A dermoscopic photograph of a skin lesion.
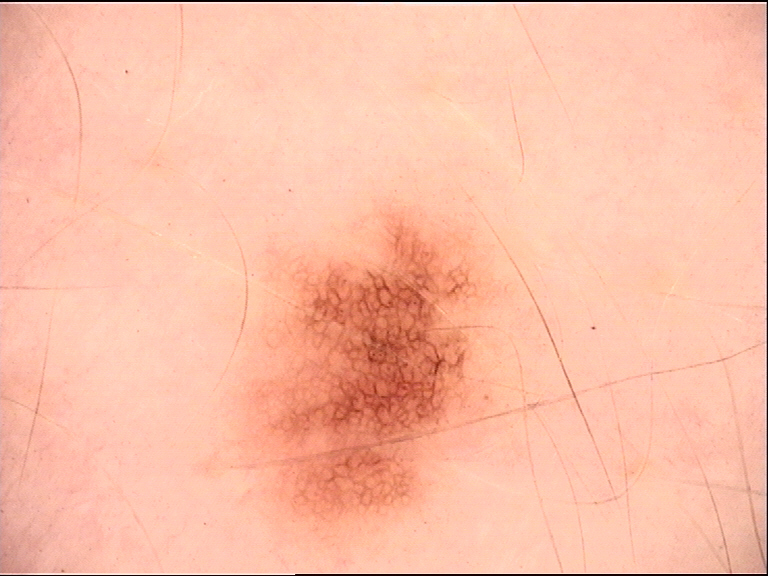Labeled as a junctional nevus.